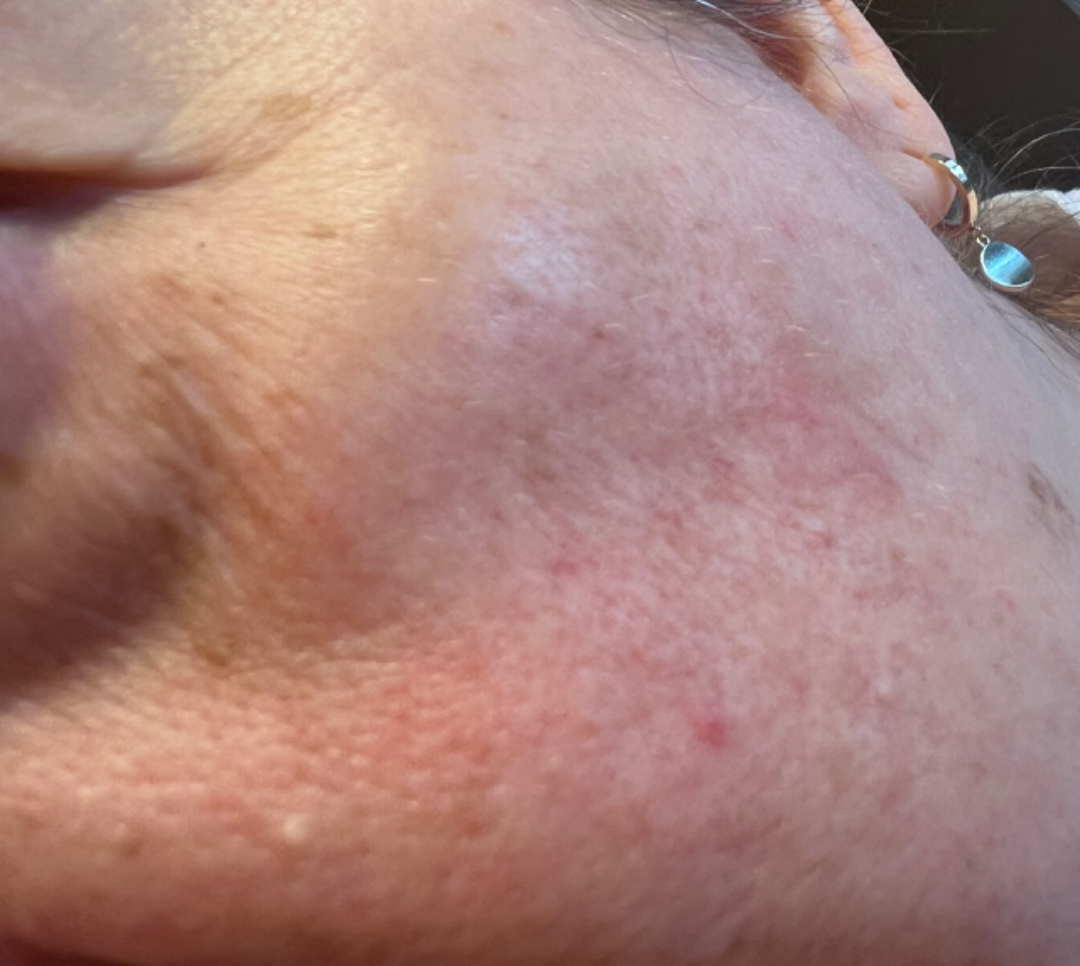No differential diagnosis could be assigned on photographic review.